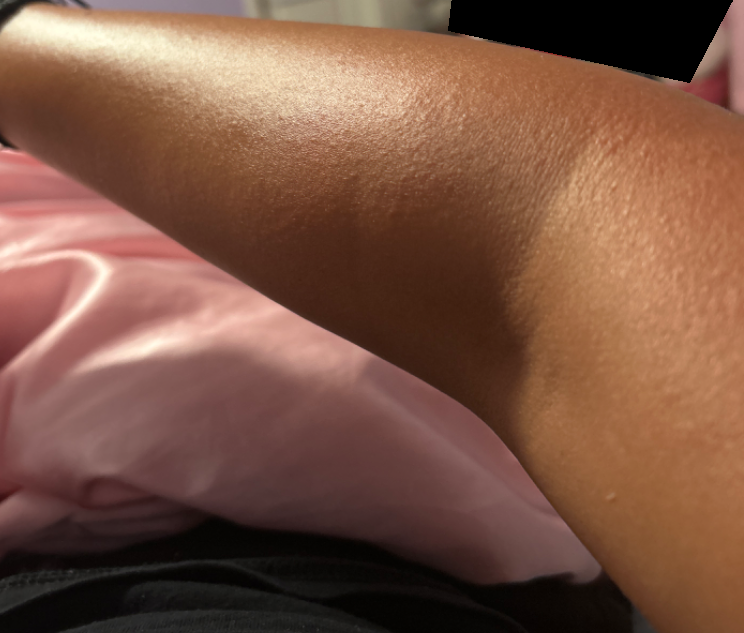assessment = not assessable